A clinical photograph showing a skin lesion.
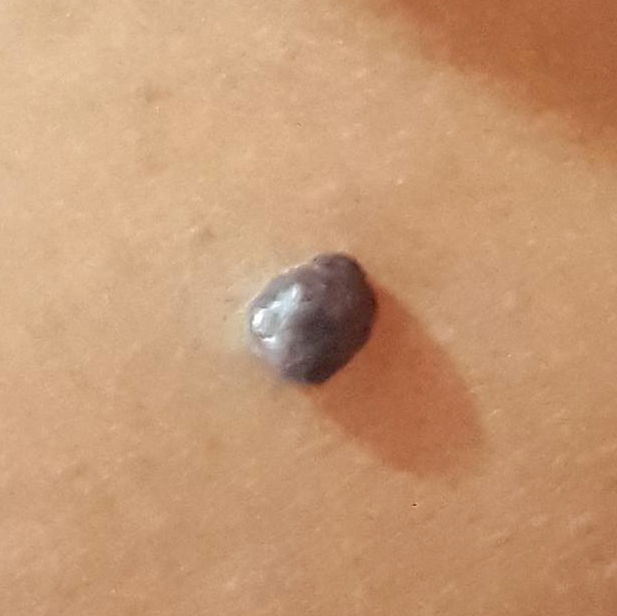The lesion was found on the abdomen.
The clinical impression was a nevus.